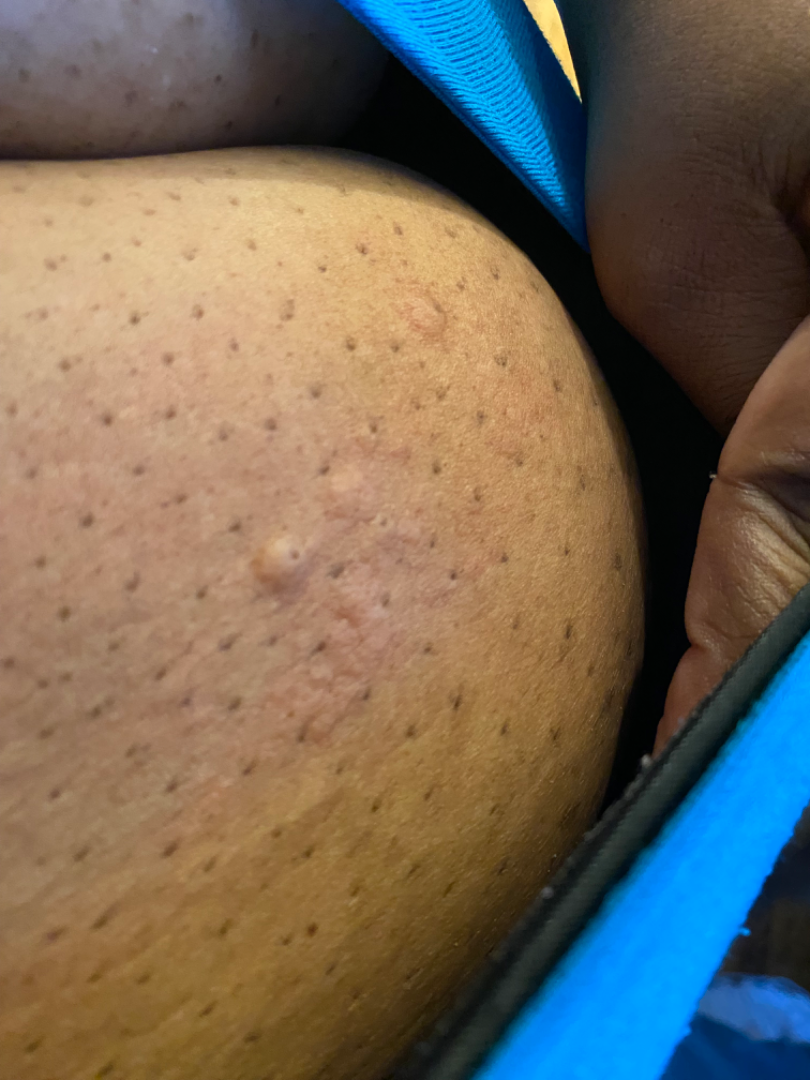Findings: The reviewing dermatologist was unable to assign a differential diagnosis from the image. Background: The affected area is the leg, back of the hand and front of the torso. Close-up view.